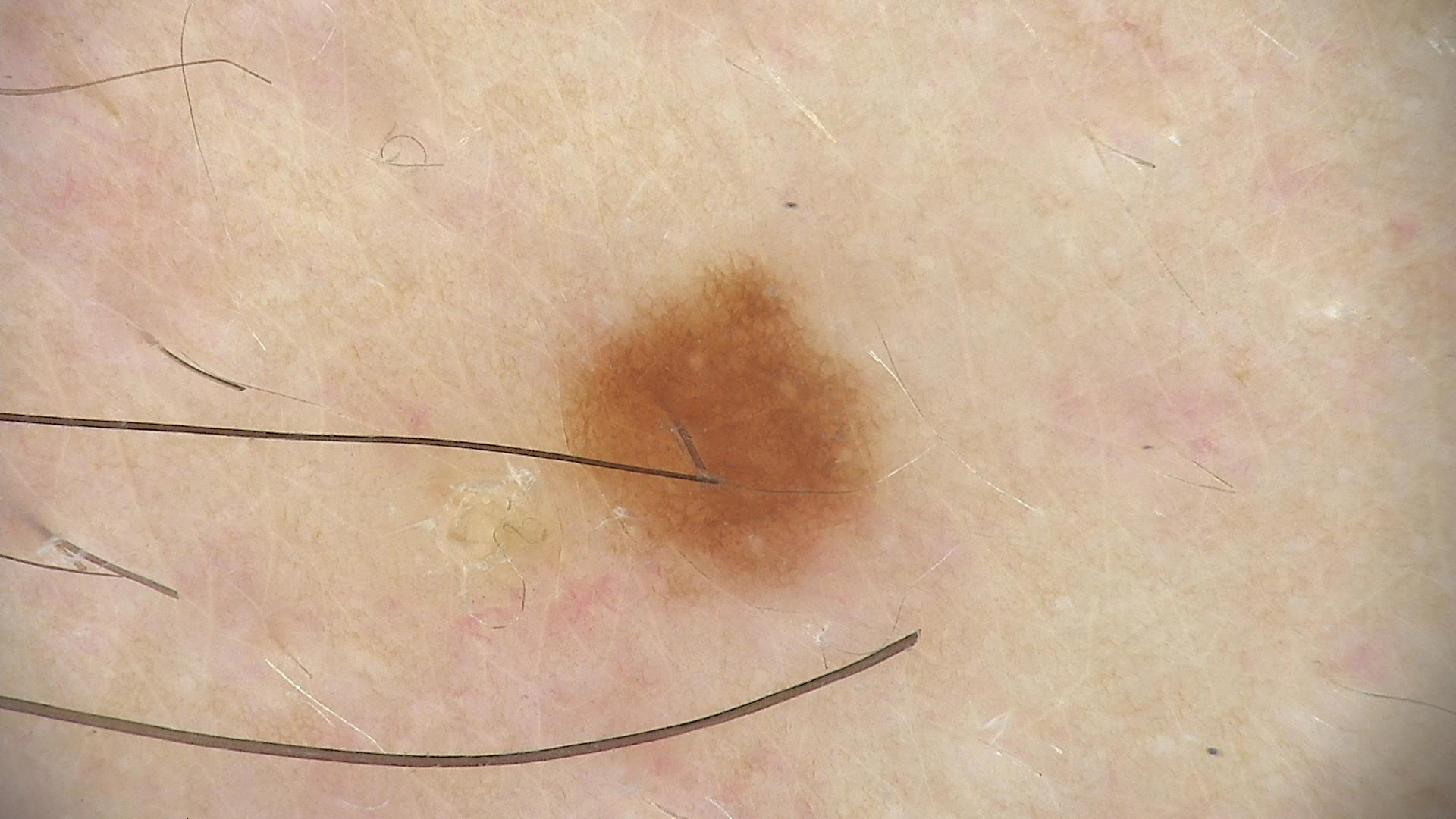image type = dermoscopy; diagnosis = dysplastic junctional nevus (expert consensus).